A female patient aged around 85 or older; Fitzpatrick phototype II; an overview clinical photograph of a skin lesion:
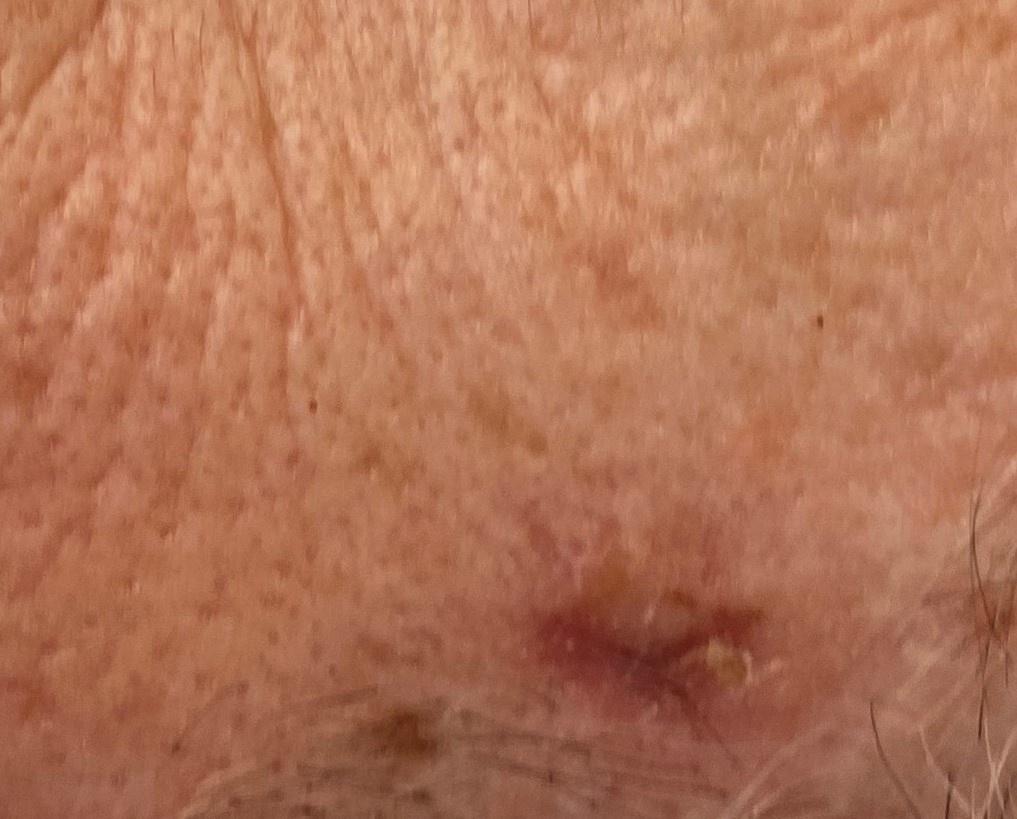The biopsy diagnosis was a malignant, adnexal lesion — a basal cell carcinoma.